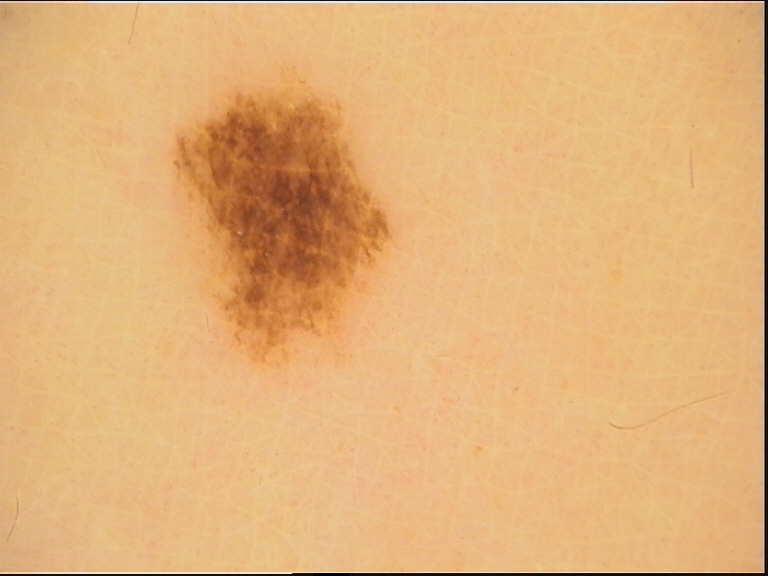Findings: A dermoscopic close-up of a skin lesion. Conclusion: The diagnostic label was a benign lesion — a dysplastic junctional nevus.